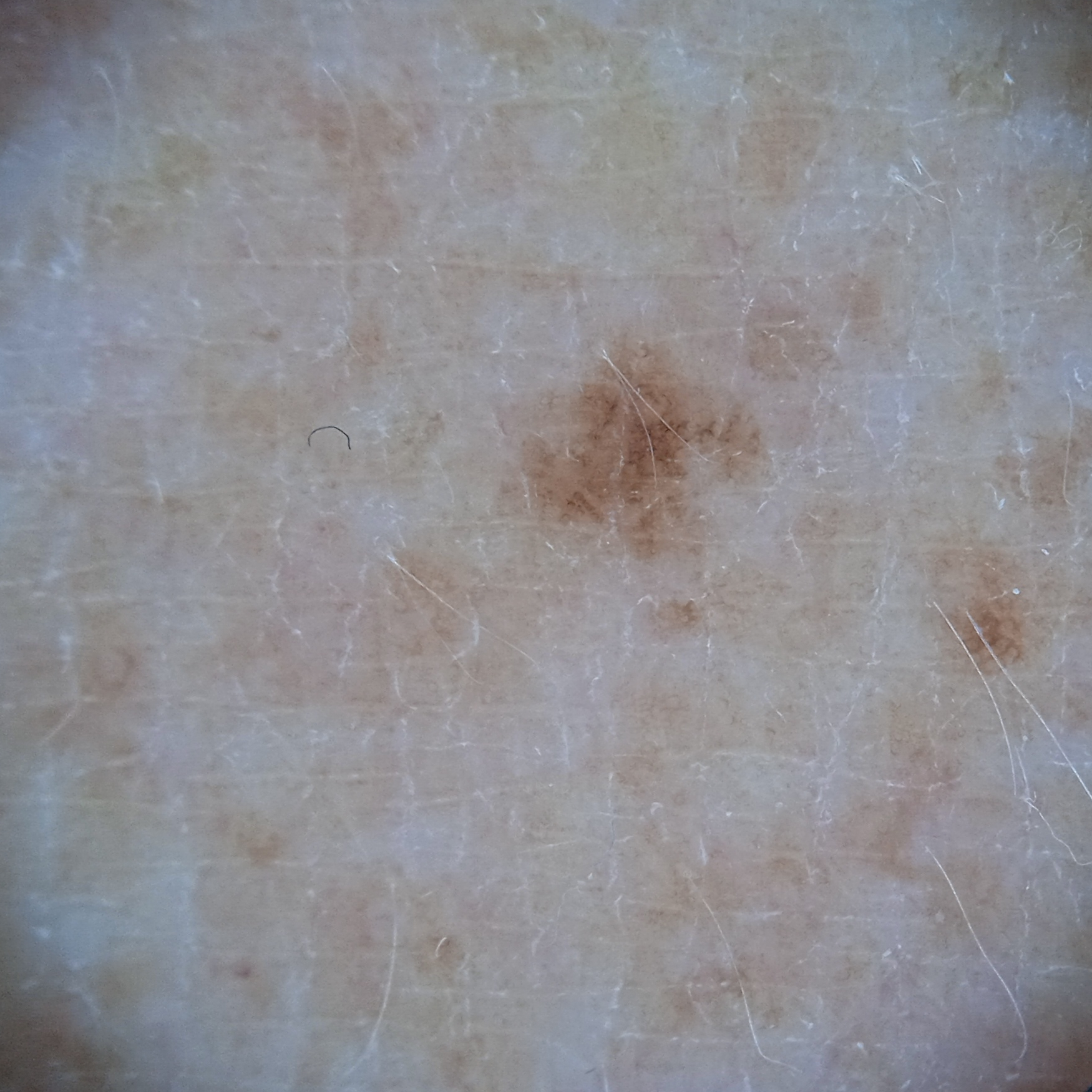Case:
– patient · male, 54 years of age
– modality · dermatoscopic image
– referral context · research study (no referral diagnosis)
– body site · an arm
– size · 2.6 mm
– assessment · melanocytic nevus (dermatologist consensus)